This is a close-up image — 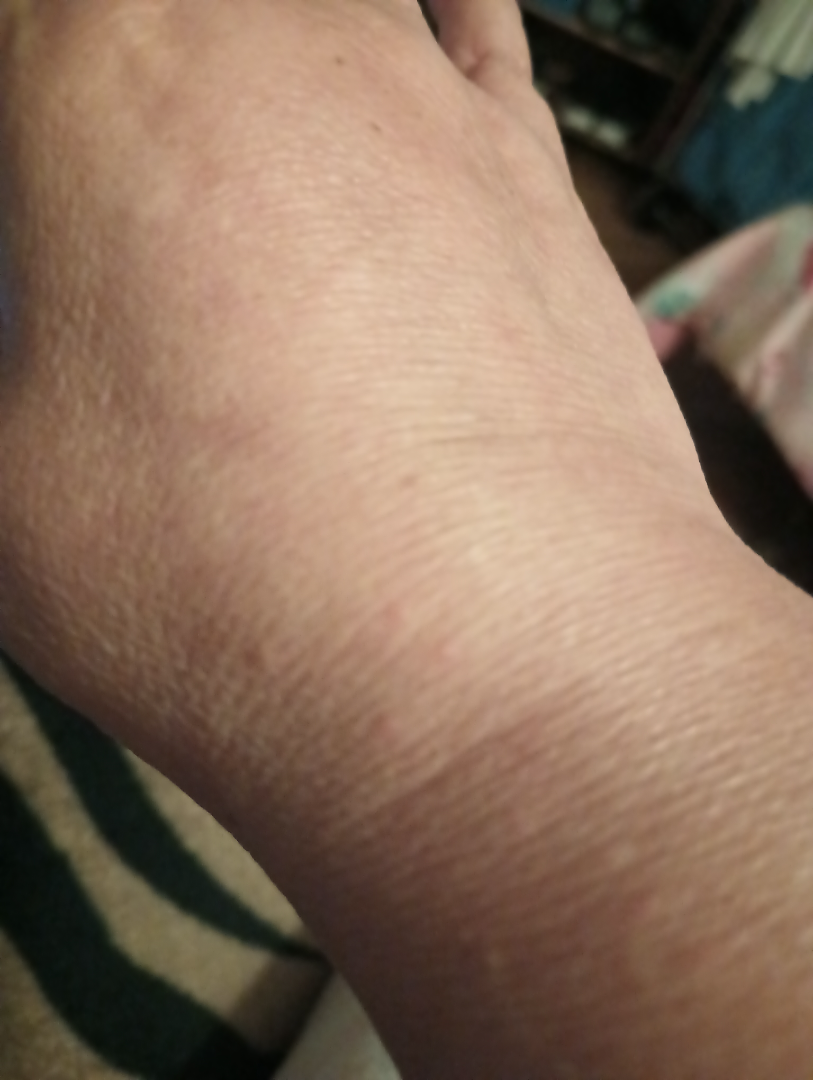assessment — ungradable on photographic review.